The patient says their skin reddens with sun exposure. The patient reports a personal history of skin cancer and a personal history of cancer. A male subject 77 years old. Imaged for a research study, with no referral diagnosis recorded. A macroscopic clinical photograph of a skin lesion — 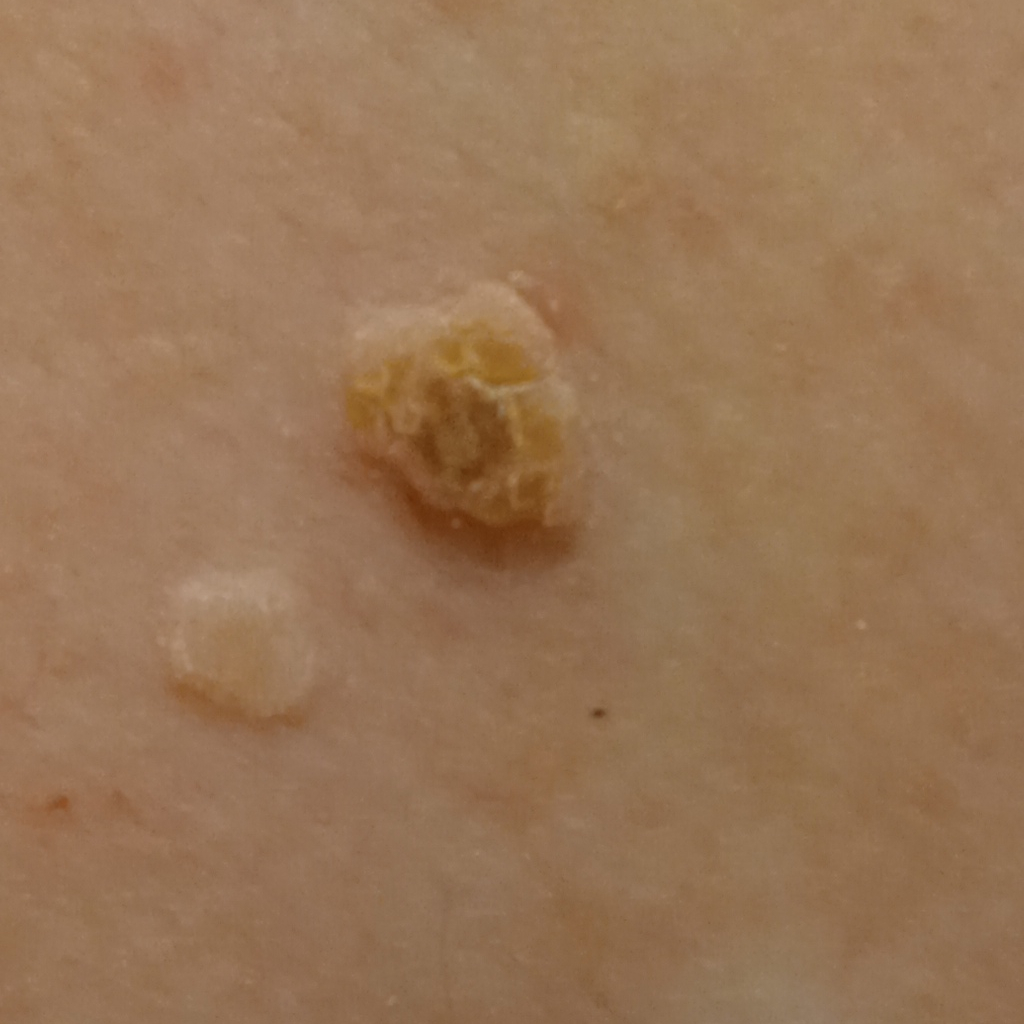Located on the back. The lesion is about 11.1 mm across. Dermatologist review favored an actinic keratosis.